Close-up view; female subject, age 18–29; the arm is involved.
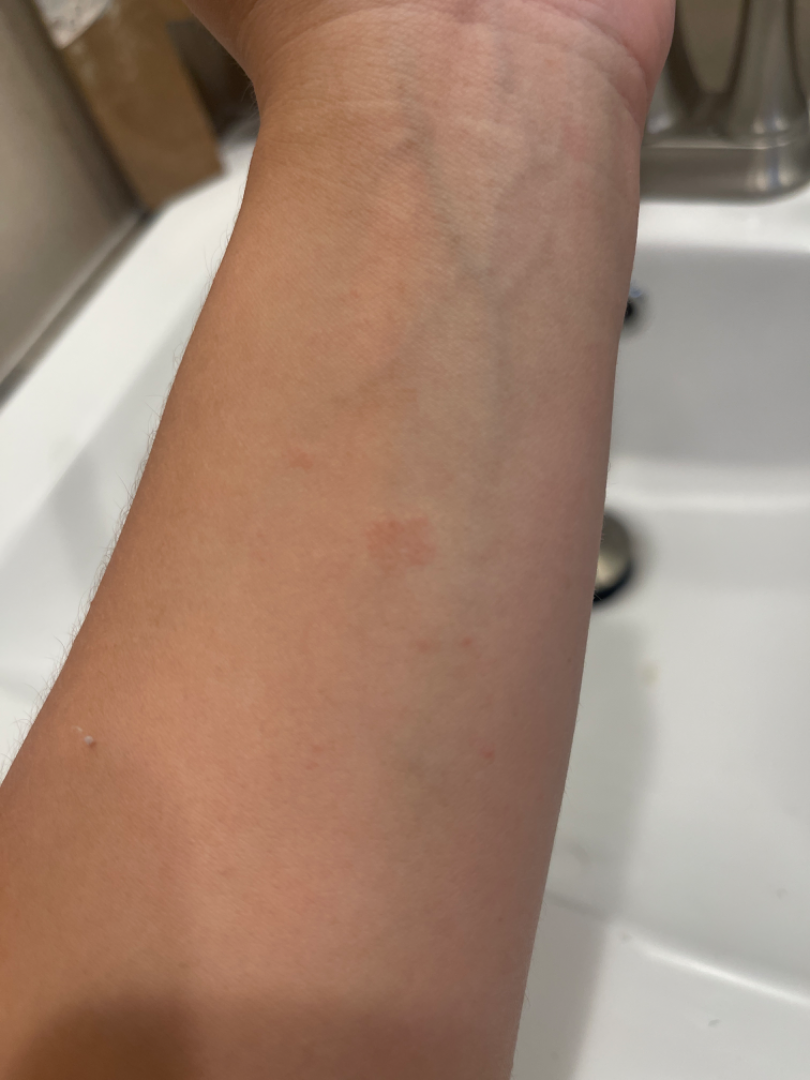Findings:
- assessment · indeterminate from the photograph
- texture · flat
- patient's own categorization · a rash
- symptom duration · one to four weeks
- lesion symptoms · none reported